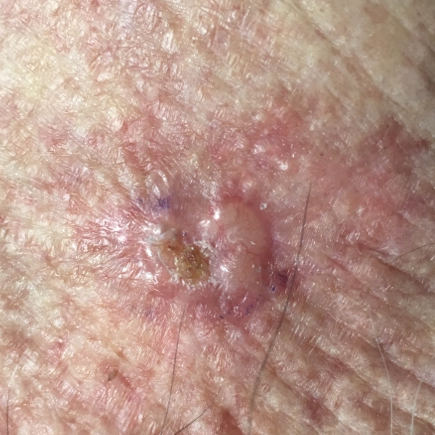Notes:
- imaging · clinical photo
- FST · II
- risk factors · alcohol use, prior malignancy (patient or family), prior skin cancer (patient or family), no pesticide exposure, no tobacco use
- subject · male, in their 60s
- region · the face
- size · 12x9 mm
- diagnostic label · basal cell carcinoma (biopsy-proven)